Close-up view.
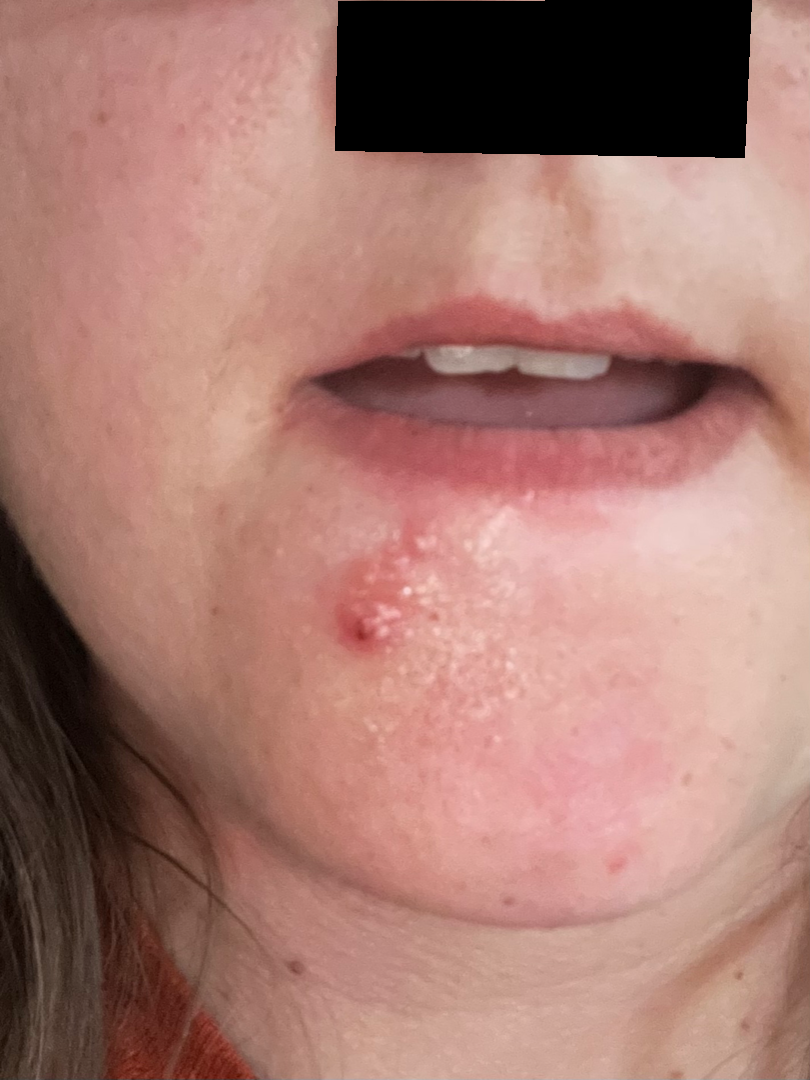Patient information:
Skin tone: FST II; human graders estimated 2 on the Monk skin tone scale. Texture is reported as raised or bumpy and fluid-filled.
Review:
On dermatologist assessment of the image: favoring Herpes Simplex; with consideration of Photodermatitis; possibly Irritant Contact Dermatitis.